The arm and leg are involved · the subject is a female aged 40–49 · the photograph was taken at an angle:
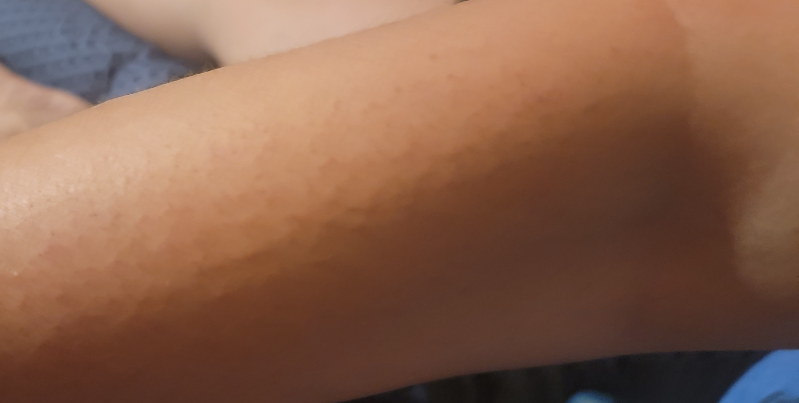Review: The reviewer was unable to grade this case for skin condition. Patient information: The condition has been present for less than one week. The patient indicates itching and burning. The patient considered this a rash. Texture is reported as raised or bumpy.